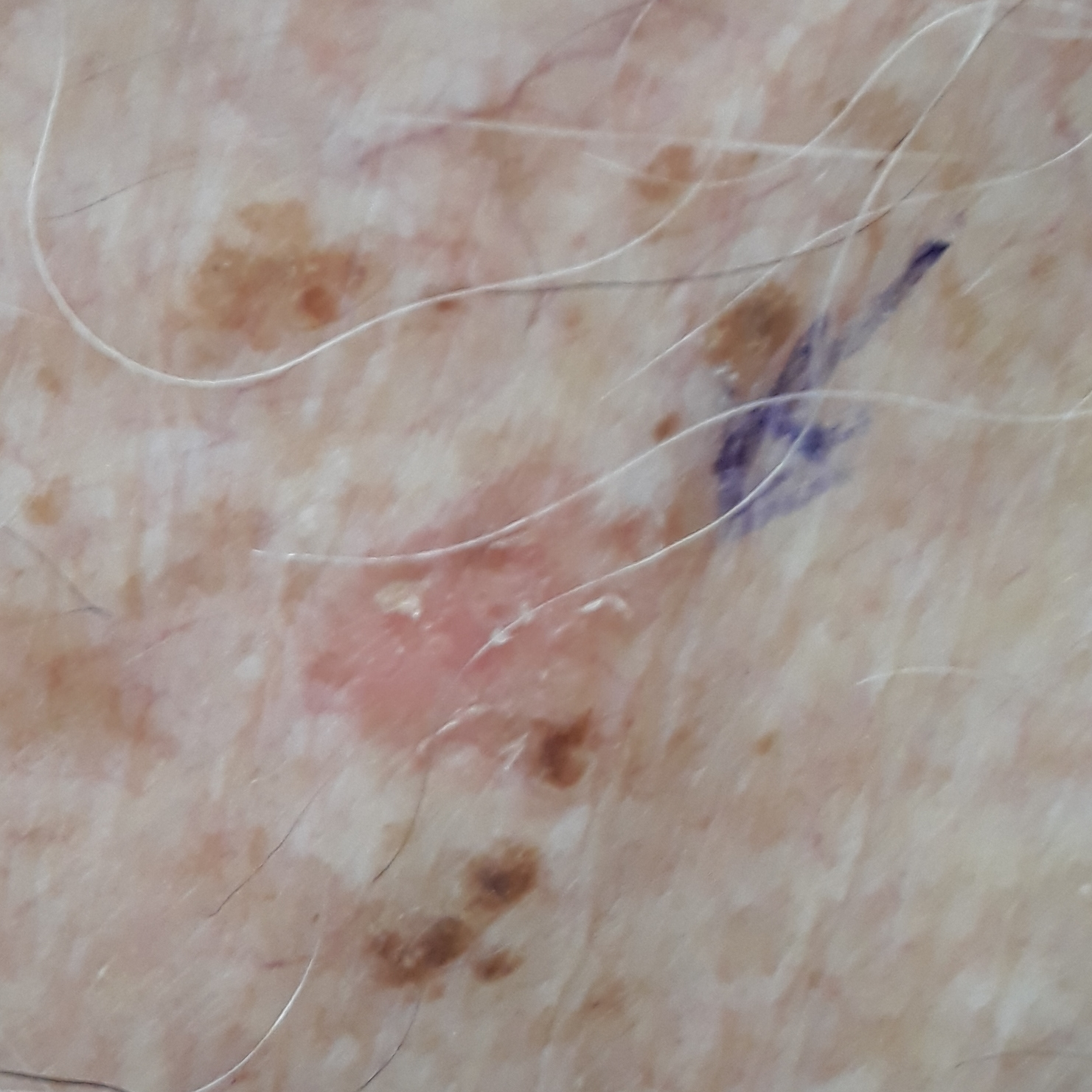A clinical photograph of a skin lesion. A male patient in their early 80s. By history, tobacco use and pesticide exposure. The patient is Fitzpatrick III. The lesion is located on the chest. The lesion measures approximately 15 × 12 mm. The patient describes that the lesion has not bled. Expert review favored a lesion with uncertain malignant potential — an actinic keratosis.